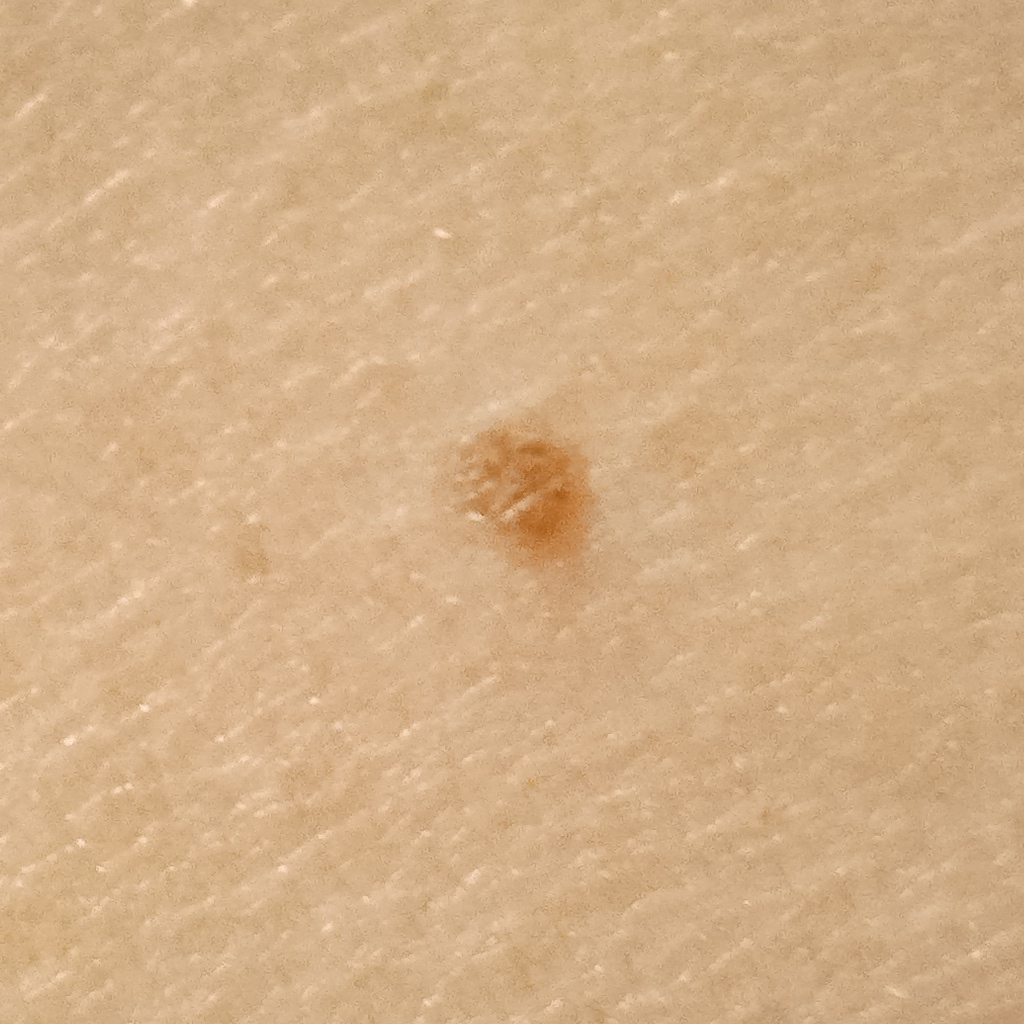{"image": "clinical photograph", "lesion_size": {"diameter_mm": 2.2}, "diagnosis": {"name": "melanocytic nevus", "malignancy": "benign"}}